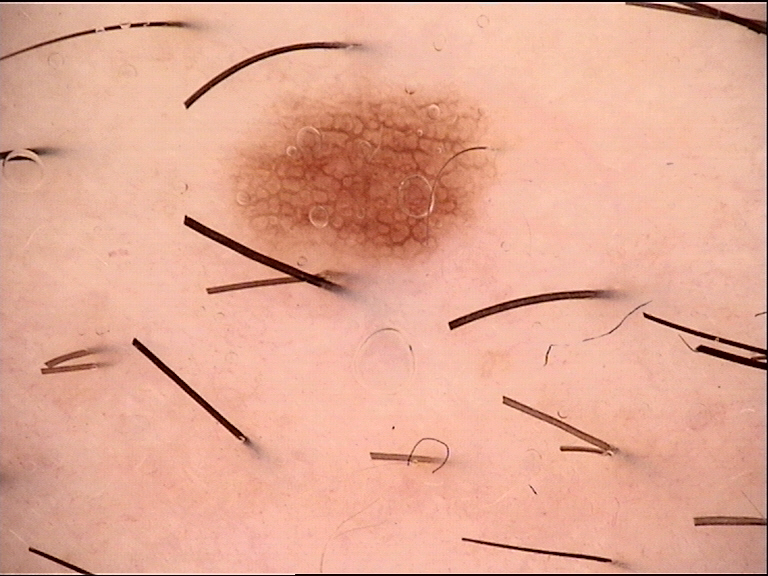{
  "image": "dermoscopy",
  "diagnosis": {
    "name": "dysplastic junctional nevus",
    "code": "jd",
    "malignancy": "benign",
    "super_class": "melanocytic",
    "confirmation": "expert consensus"
  }
}